A skin lesion imaged with a dermatoscope.
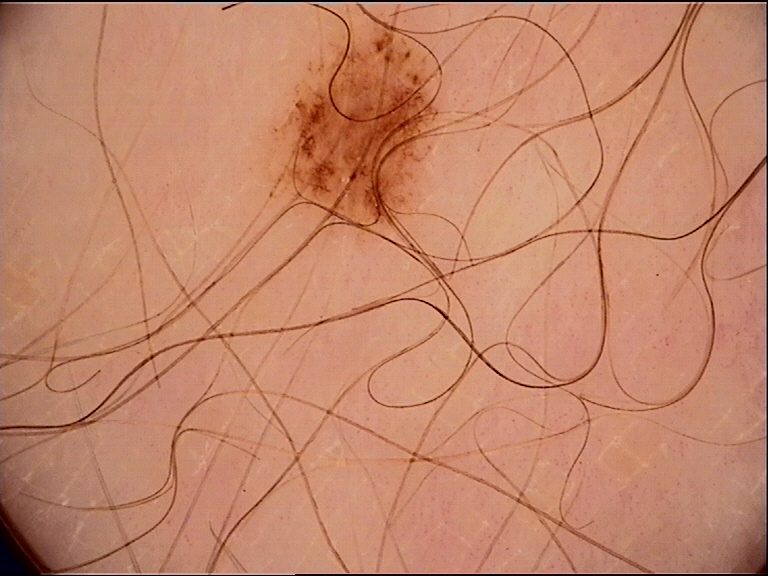Labeled as a benign lesion — a dysplastic junctional nevus.